A dermoscopic close-up of a skin lesion.
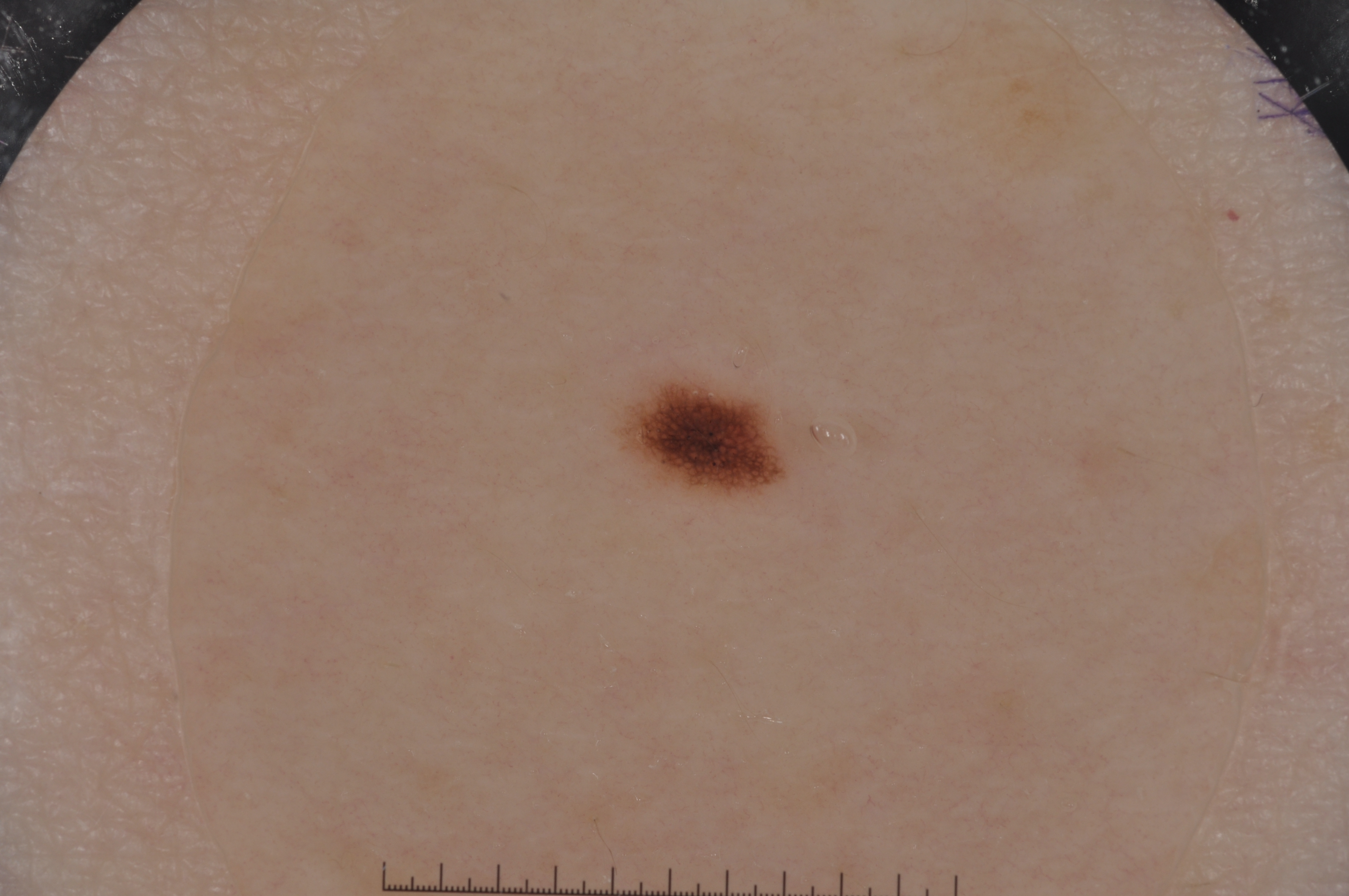Image and clinical context: Dermoscopic review identifies pigment network. With coordinates (x1, y1, x2, y2), the lesion's extent is 611, 371, 803, 497. Impression: The diagnostic assessment was a melanocytic nevus, a benign lesion.